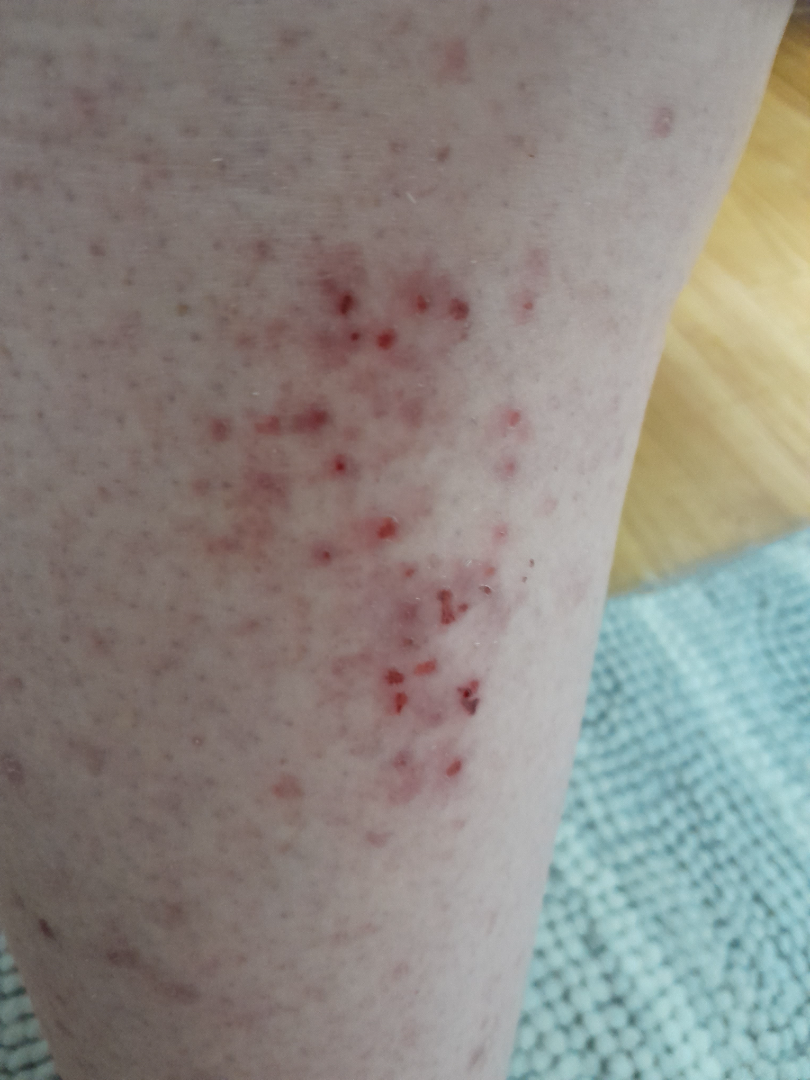The skin findings could not be characterized from the image.
The lesion involves the leg.
The photo was captured at a distance.